A dermoscopic close-up of a skin lesion:
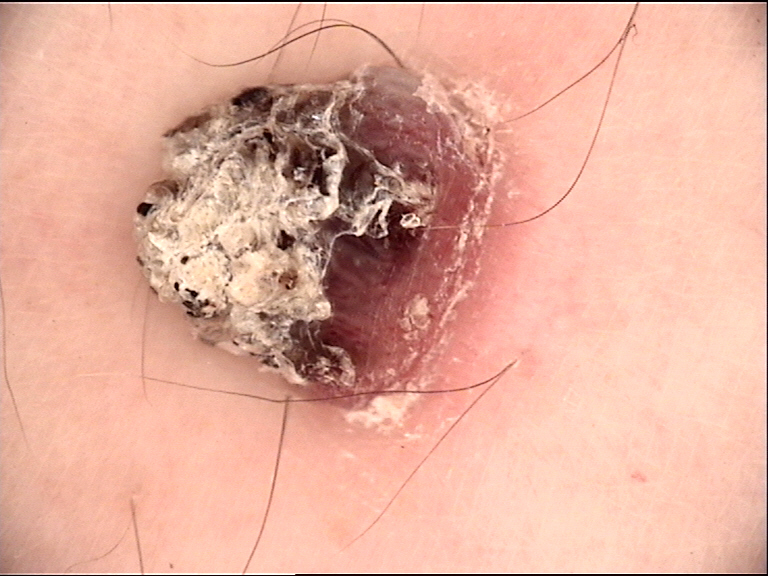Findings:
– category · keratinocytic
– pathology · cutaneous horn (biopsy-proven)